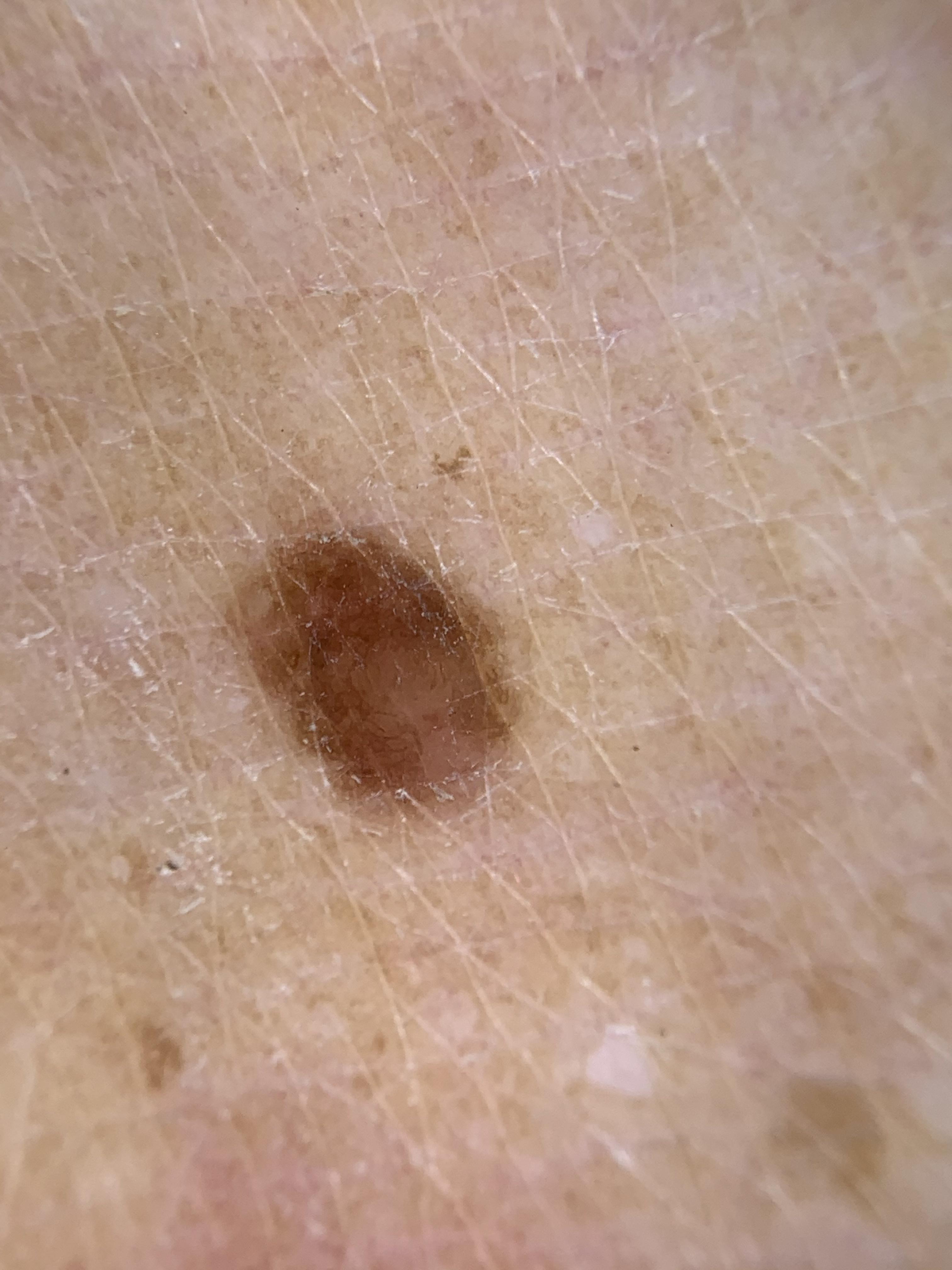Histopathologically confirmed as a nevus.